The photograph was taken at a distance. The contributor is 40–49, male. The affected area is the leg: 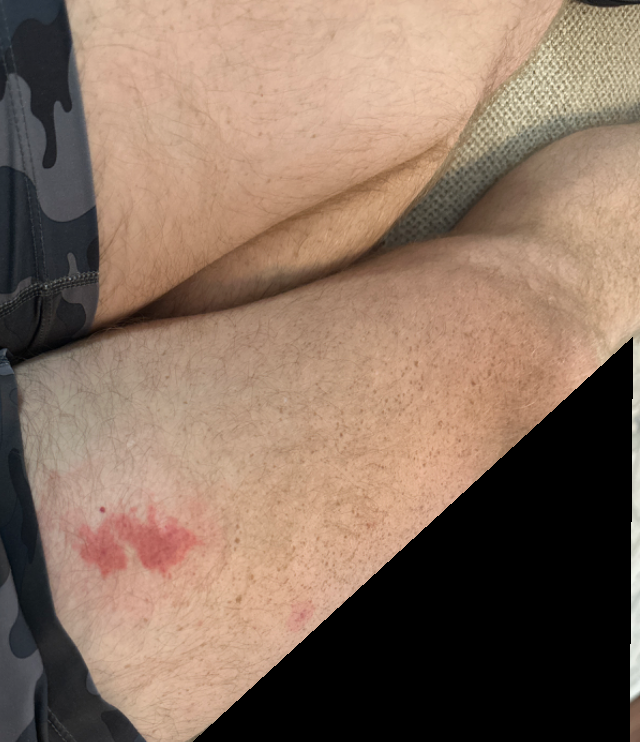Background: The patient considered this a rash. Reported duration is less than one week. Skin tone: FST II; non-clinician graders estimated Monk Skin Tone 2 or 4 (two reviewer pools disagreed). The patient reported no systemic symptoms. The contributor reports the lesion is raised or bumpy. The lesion is associated with itching. Findings: The differential includes Inflammatory dermatosis and SCC/SCCIS, with no clear leading consideration; less likely is Skin and soft tissue atypical mycobacterial infection.